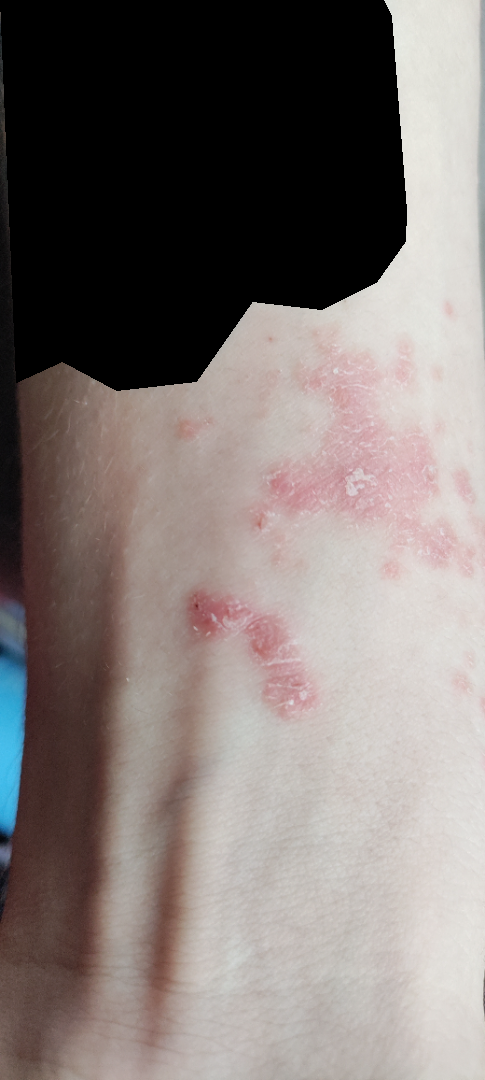onset: less than one week
surface texture: raised or bumpy and rough or flaky
view: close-up
symptoms: bothersome appearance and itching
location: arm and palm
differential: most likely Psoriasis; with consideration of Eczema; possibly Lichen planus/lichenoid eruption